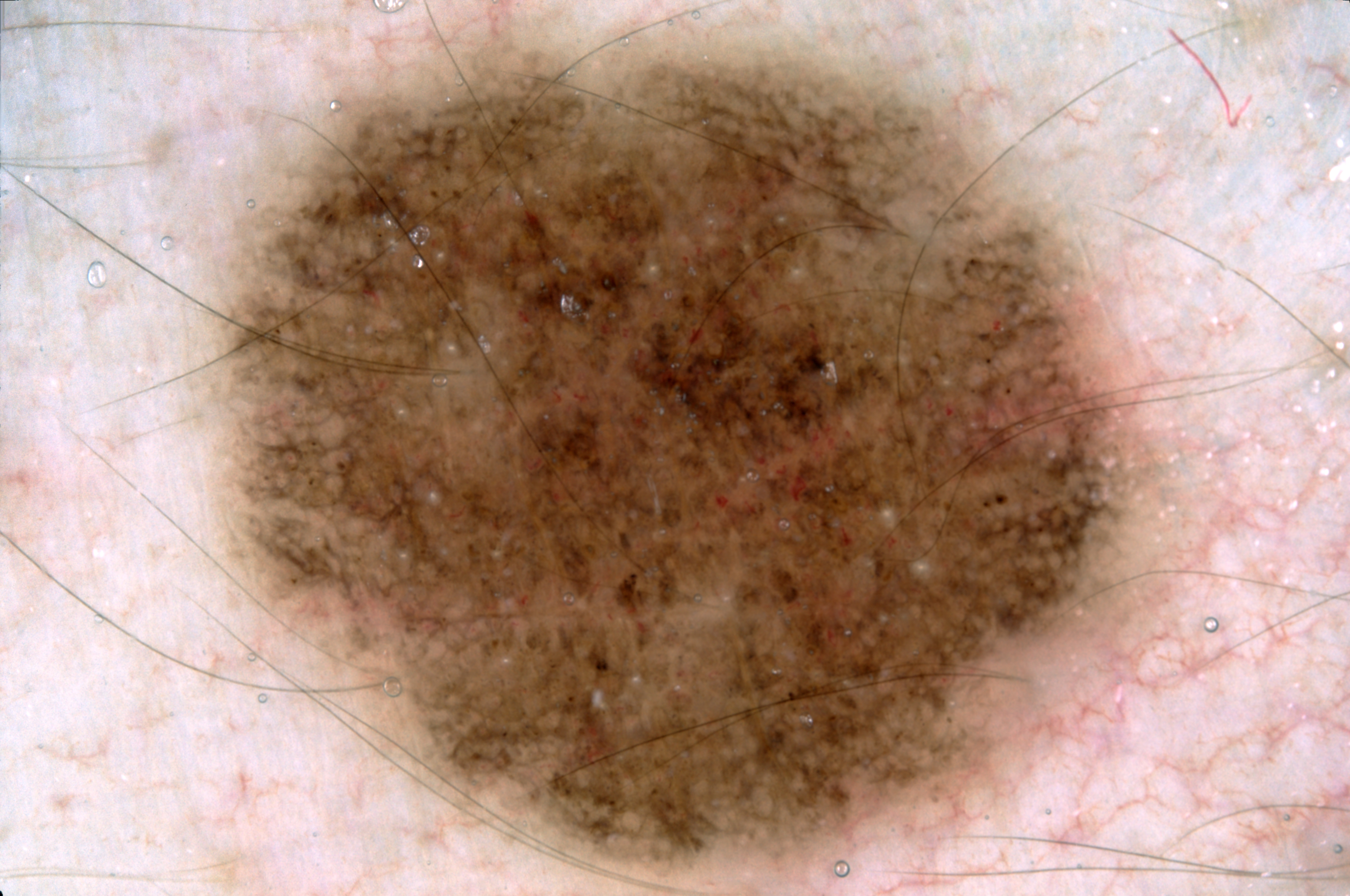<case>
<image>
  <modality>dermoscopy</modality>
</image>
<lesion_location>
  <bbox_xyxy>206, 27, 1161, 877</bbox_xyxy>
</lesion_location>
<dermoscopic_features>
  <present>pigment network, milia-like cysts</present>
  <absent>streaks, negative network</absent>
</dermoscopic_features>
<diagnosis>
  <name>melanocytic nevus</name>
  <malignancy>benign</malignancy>
  <lineage>melanocytic</lineage>
  <provenance>clinical</provenance>
</diagnosis>
</case>